A skin lesion imaged with a dermatoscope.
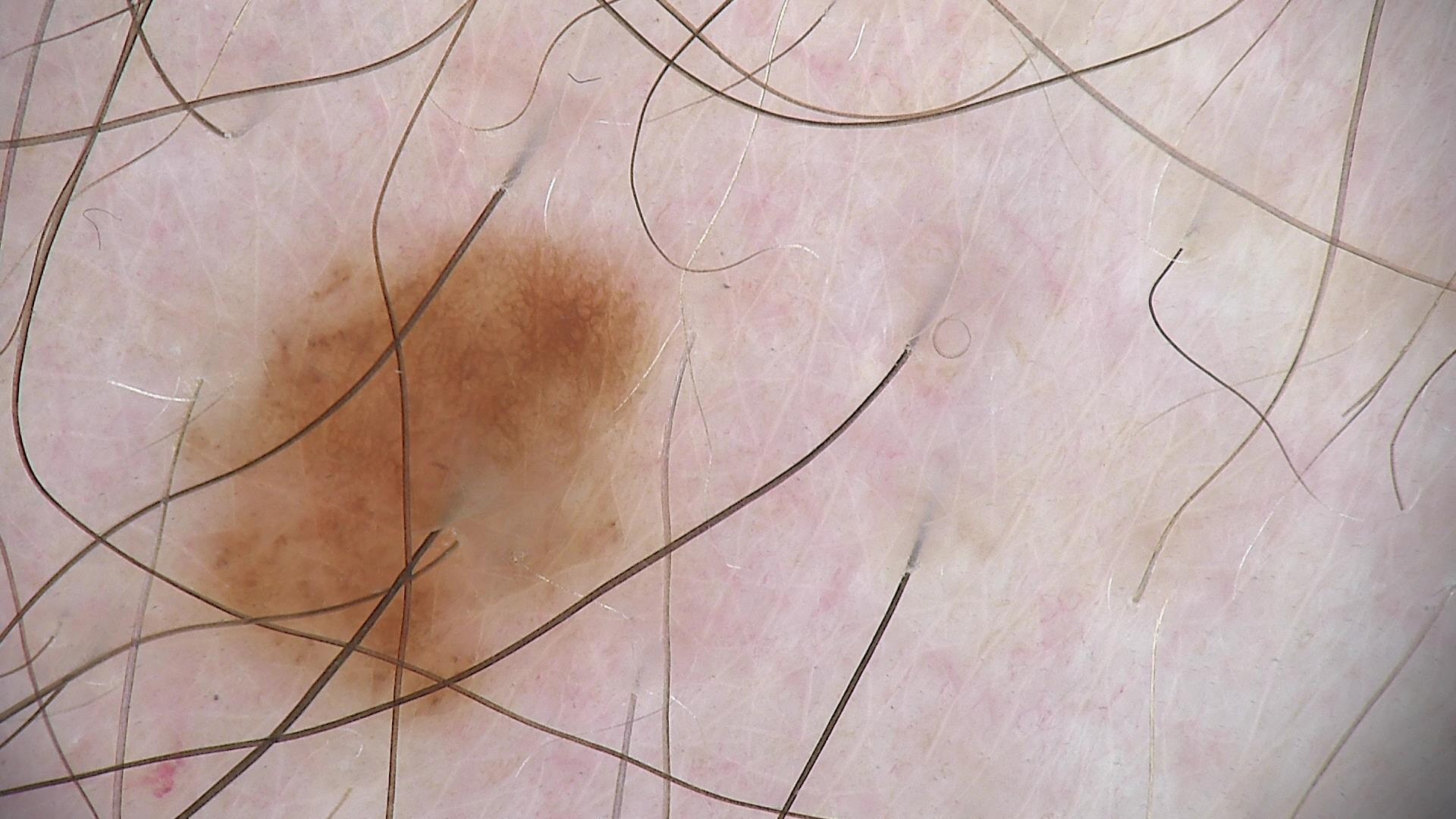The diagnosis was a dysplastic junctional nevus.